This is a close-up image — 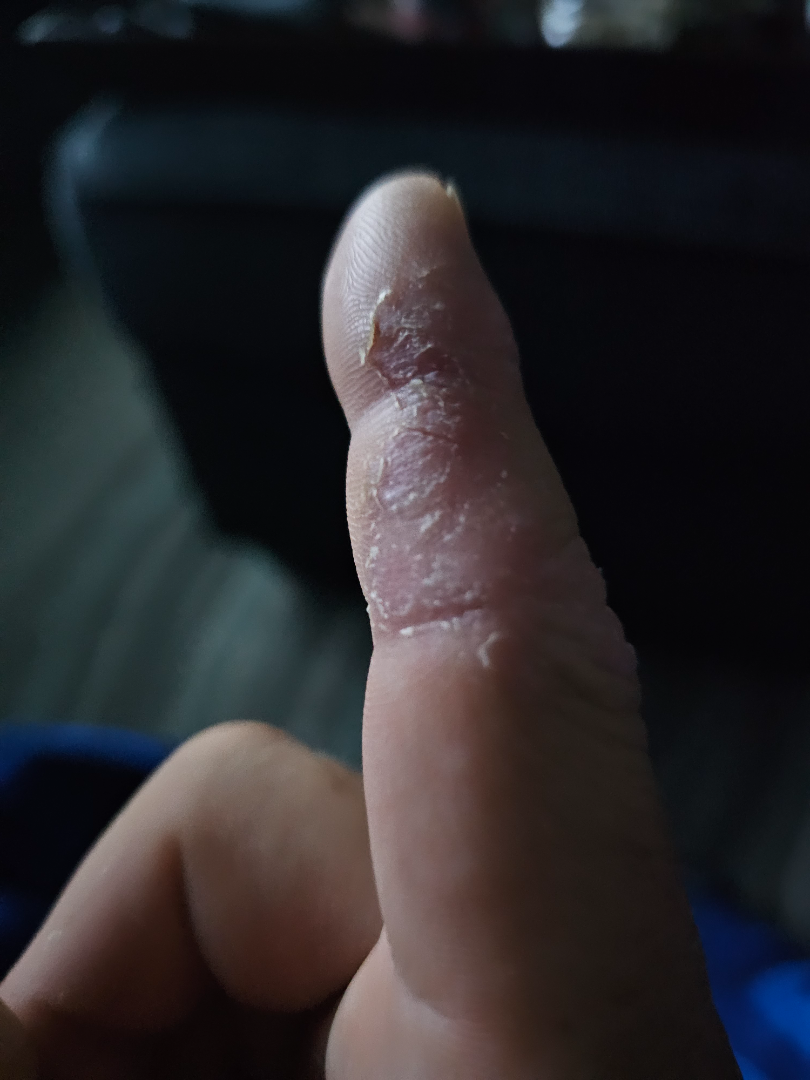Q: What is the dermatologist's impression?
A: in keeping with Eczema